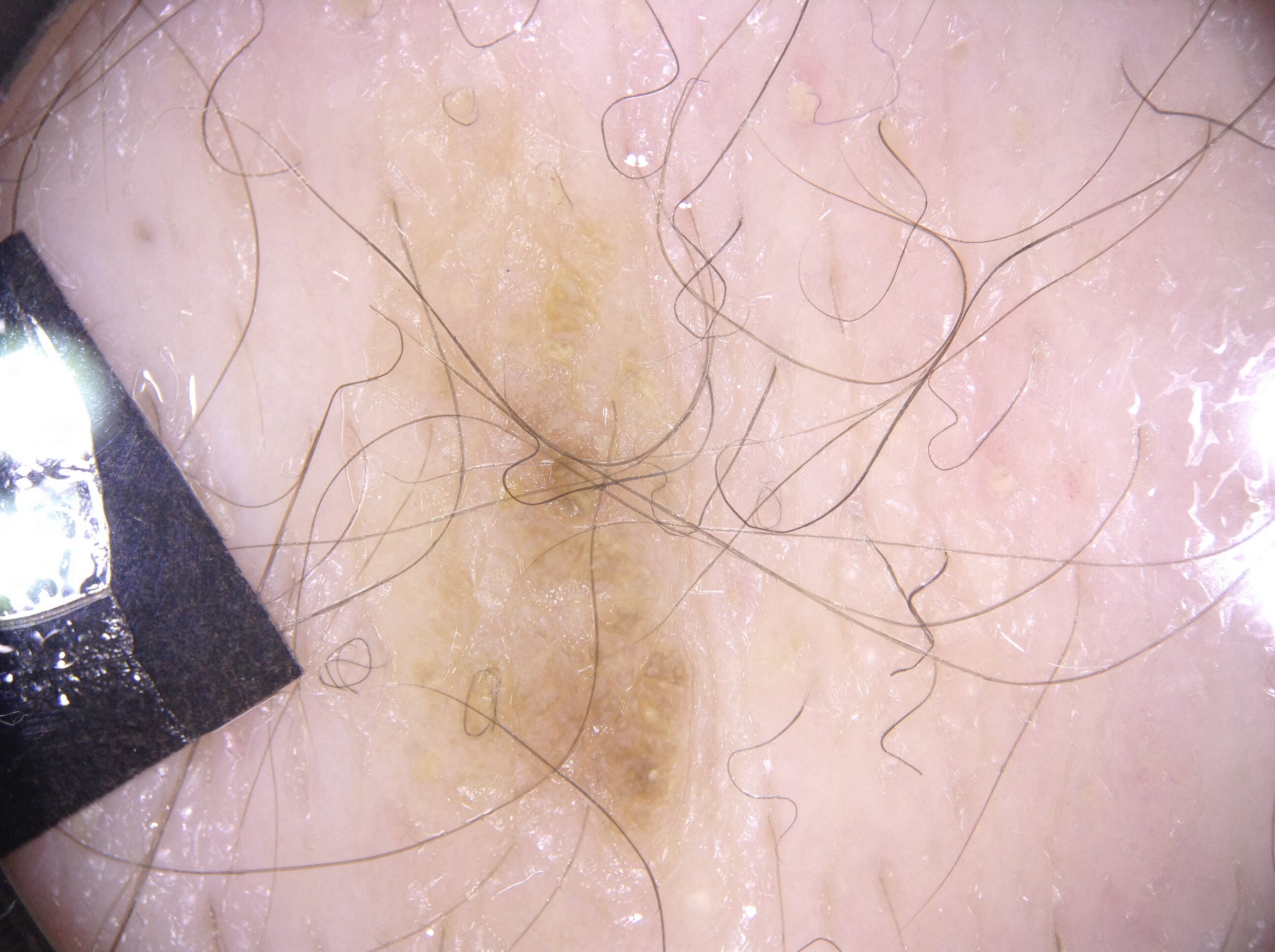<record>
  <image>
    <modality>dermoscopy</modality>
  </image>
  <patient>
    <sex>male</sex>
    <age_approx>60</age_approx>
  </patient>
  <dermoscopic_features>
    <present>milia-like cysts</present>
    <absent>pigment network, negative network, streaks</absent>
  </dermoscopic_features>
  <lesion_location>
    <bbox_xyxy>326, 46, 710, 900</bbox_xyxy>
  </lesion_location>
  <diagnosis>
    <name>seborrheic keratosis</name>
    <malignancy>benign</malignancy>
    <lineage>keratinocytic</lineage>
    <provenance>clinical</provenance>
  </diagnosis>
</record>